A dermoscopy image of a single skin lesion.
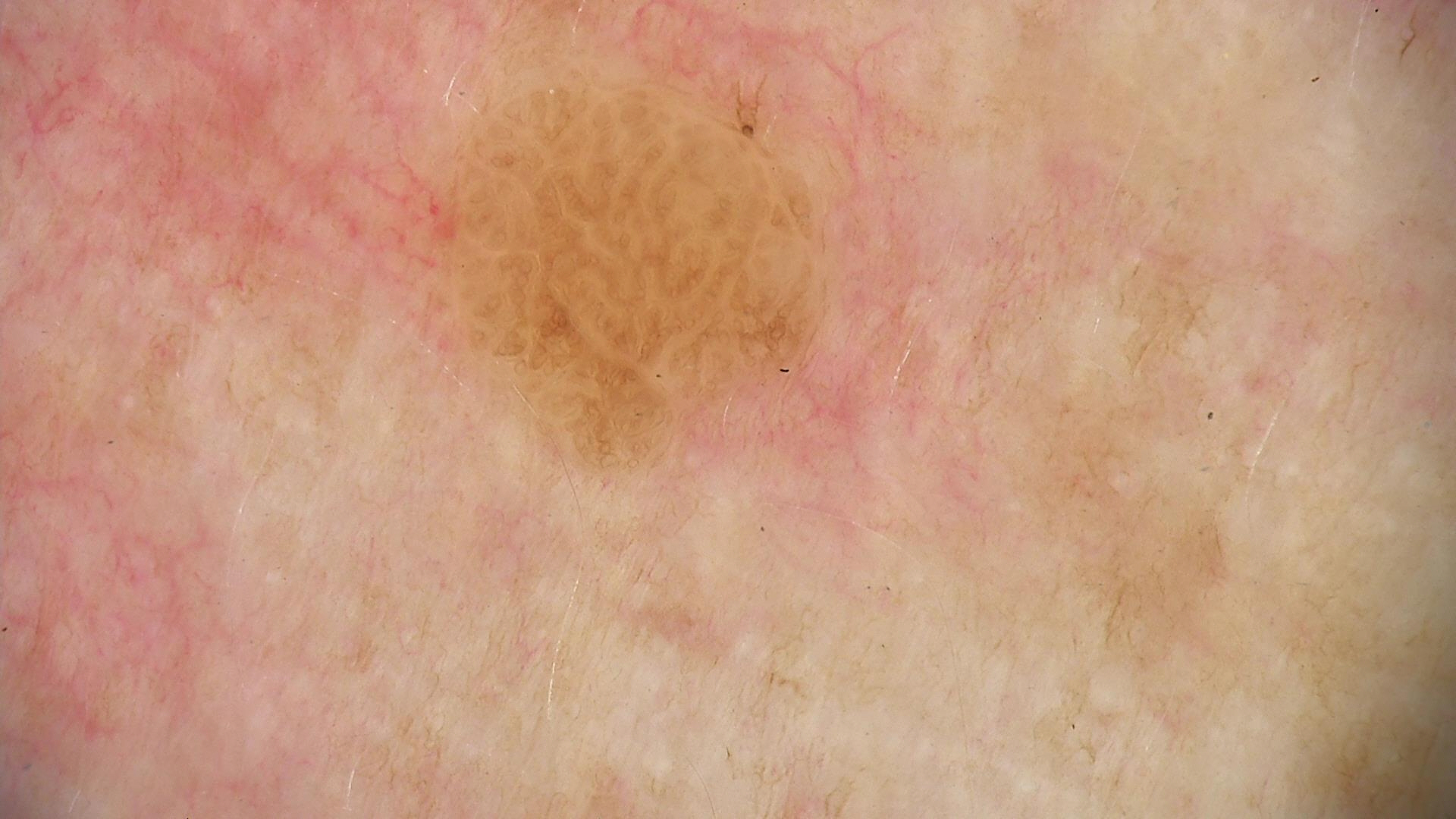<lesion>
  <lesion_type>
    <main_class>keratinocytic</main_class>
  </lesion_type>
  <diagnosis>
    <name>seborrheic keratosis</name>
    <code>sk</code>
    <malignancy>benign</malignancy>
    <super_class>non-melanocytic</super_class>
    <confirmation>expert consensus</confirmation>
  </diagnosis>
</lesion>